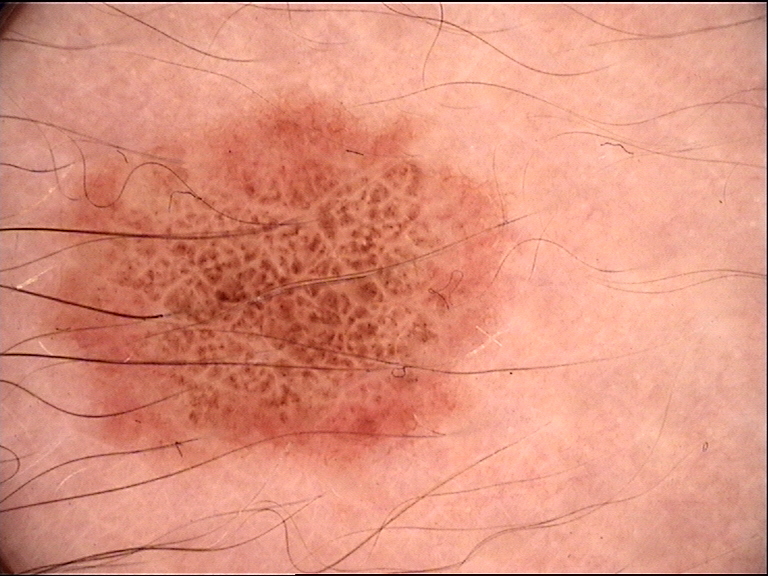A dermoscopic close-up of a skin lesion. Classified as a benign lesion — a dysplastic compound nevus.